Dermoscopy of a skin lesion: 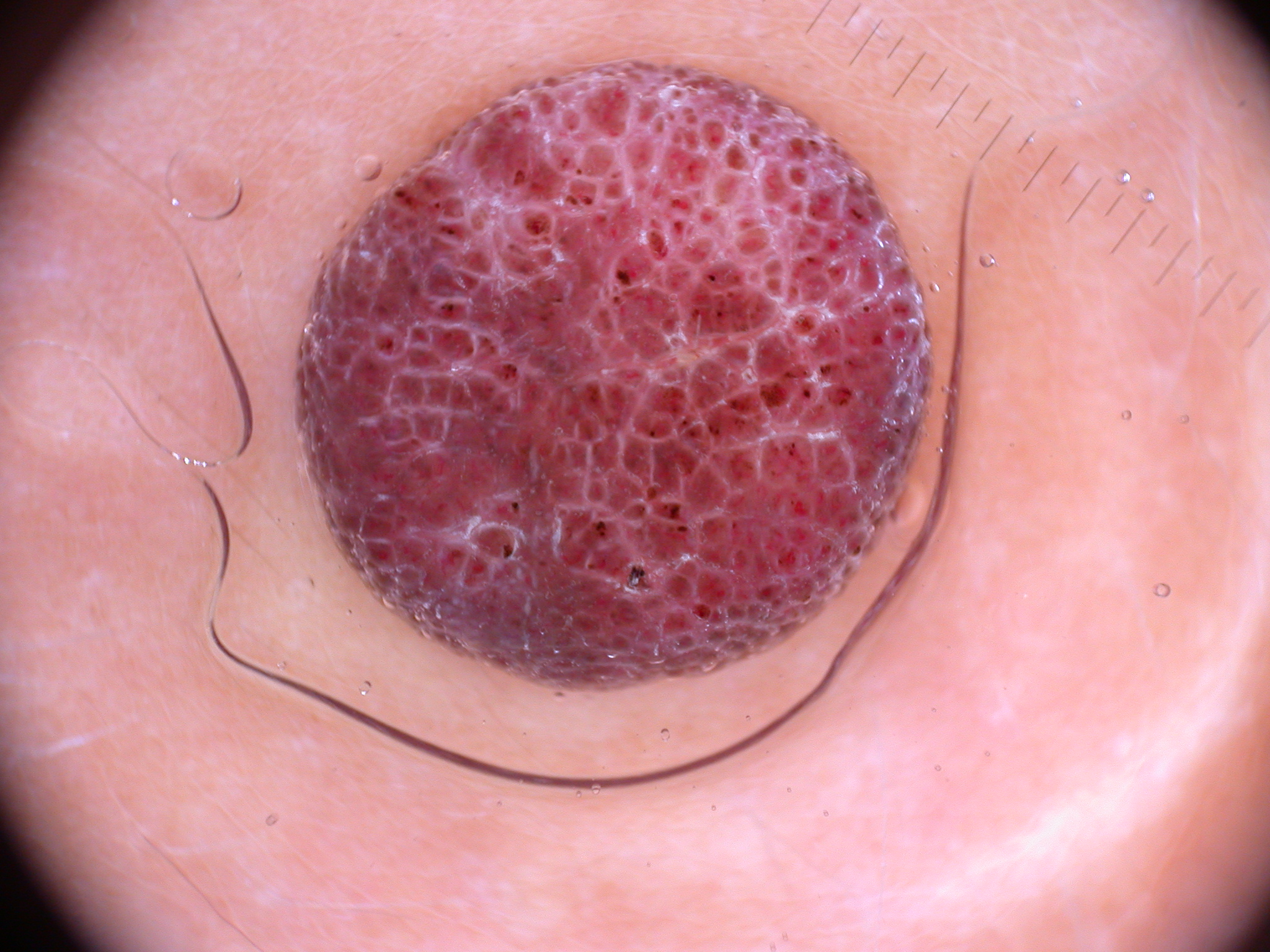<lesion>
<dermoscopic_features>
  <present/>
  <absent>streaks, pigment network, globules, milia-like cysts, negative network</absent>
</dermoscopic_features>
<lesion_location>
  <bbox_xyxy>290, 60, 935, 689</bbox_xyxy>
</lesion_location>
<lesion_extent>moderate</lesion_extent>
<diagnosis>
  <name>melanocytic nevus</name>
  <malignancy>benign</malignancy>
  <lineage>melanocytic</lineage>
  <provenance>clinical</provenance>
</diagnosis>
</lesion>